This image was taken at an angle · female contributor, age 40–49 · located on the palm and back of the hand:
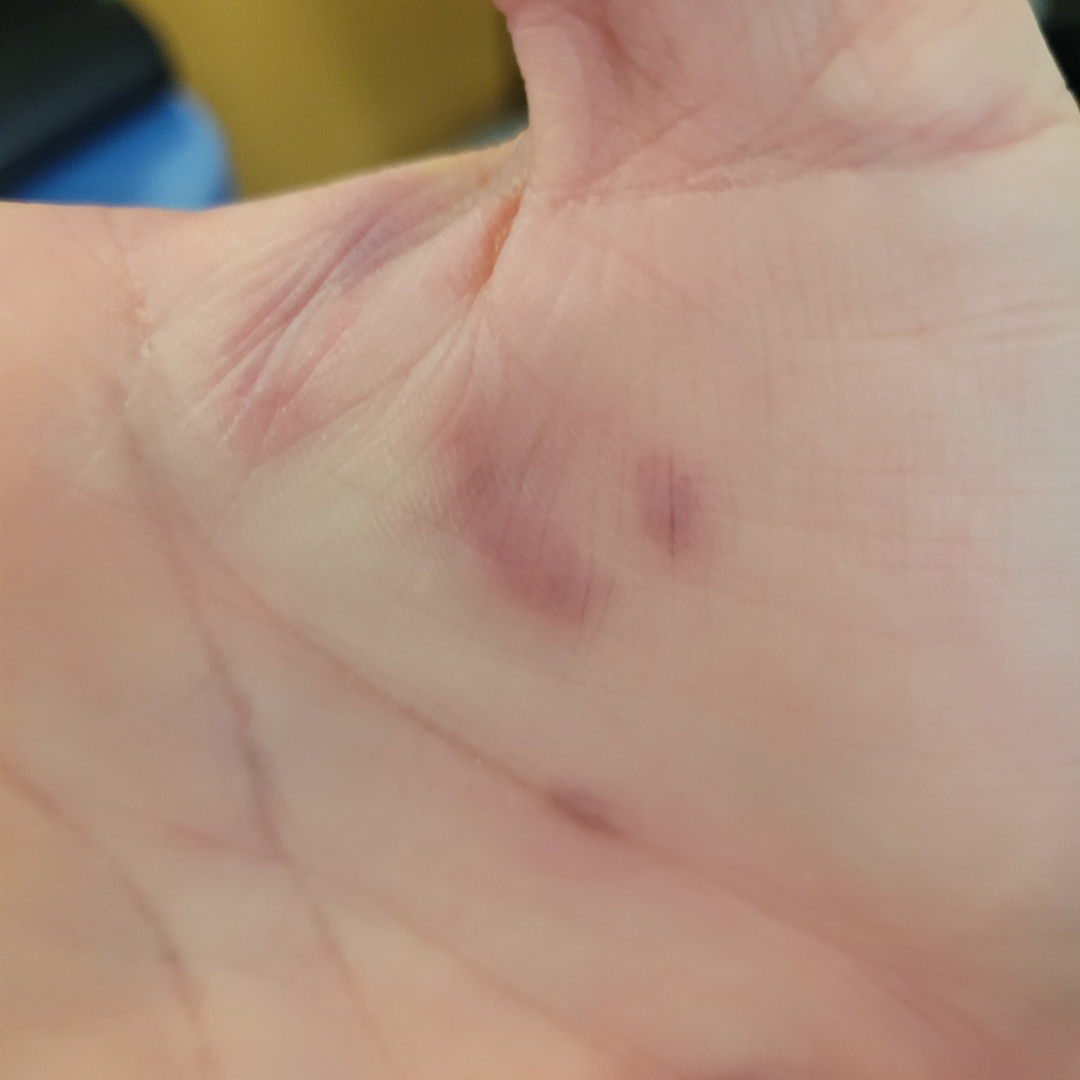differential:
  tied_lead:
    - Tinea
    - Burn of skin
    - Allergic Contact Dermatitis